The subject is a male aged 83 or older, a skin lesion imaged with a dermatoscope.
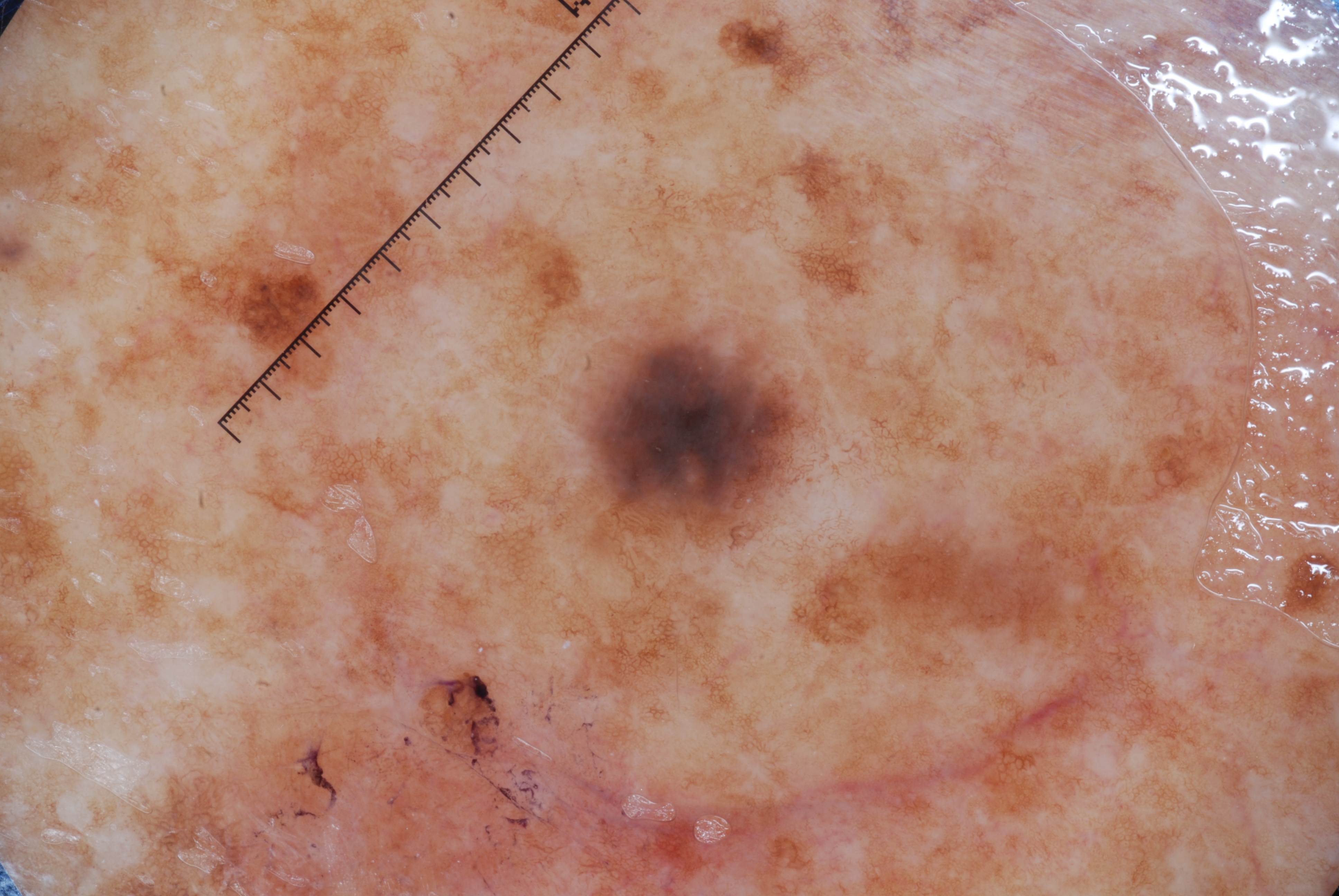dermoscopic findings = milia-like cysts; absent: pigment network, negative network, and streaks | lesion location = bbox=[570, 317, 809, 561] | diagnostic label = a melanocytic nevus, a benign lesion.